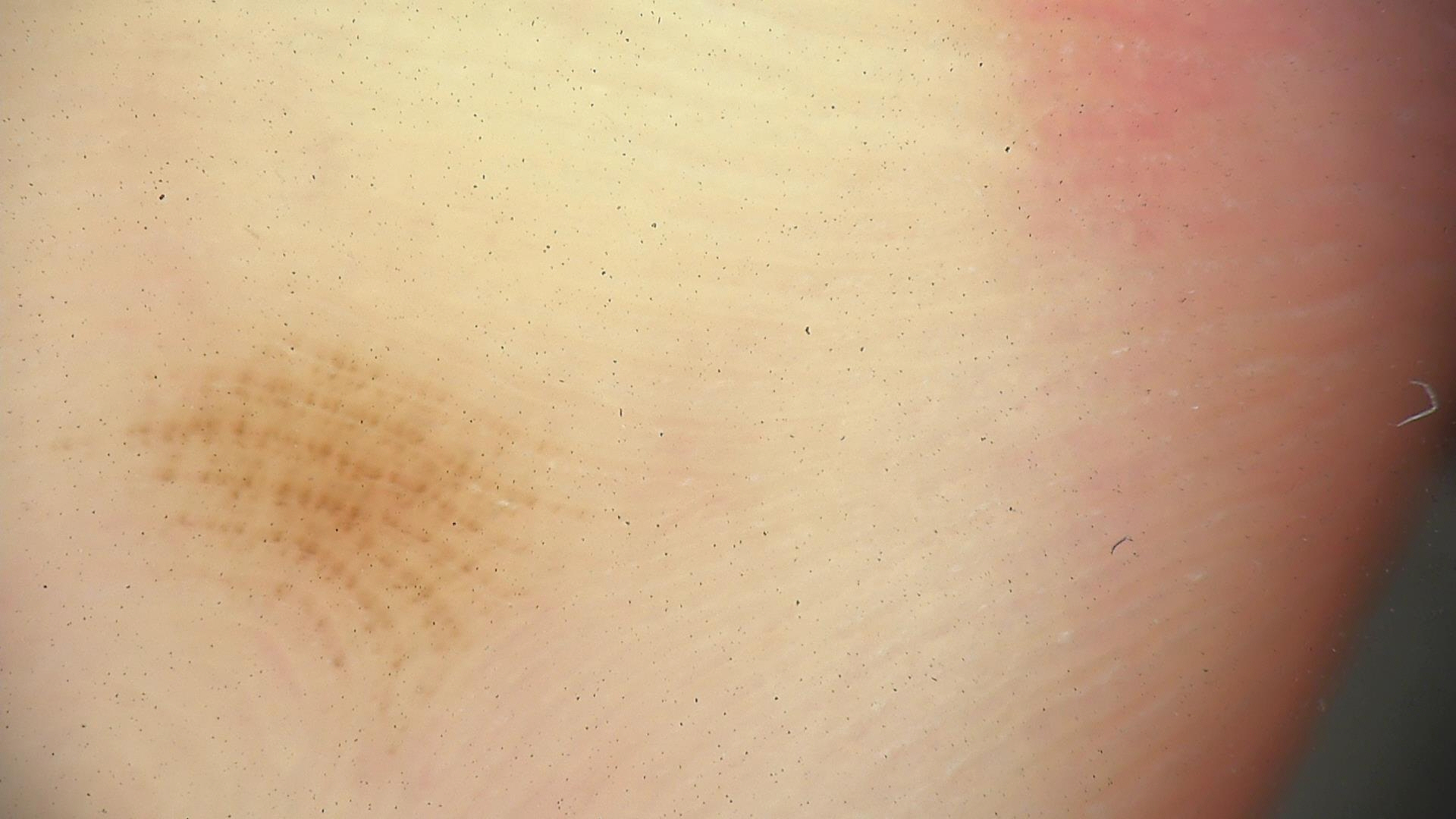A dermoscopic image of a skin lesion. The diagnosis was a benign lesion — an acral dysplastic junctional nevus.